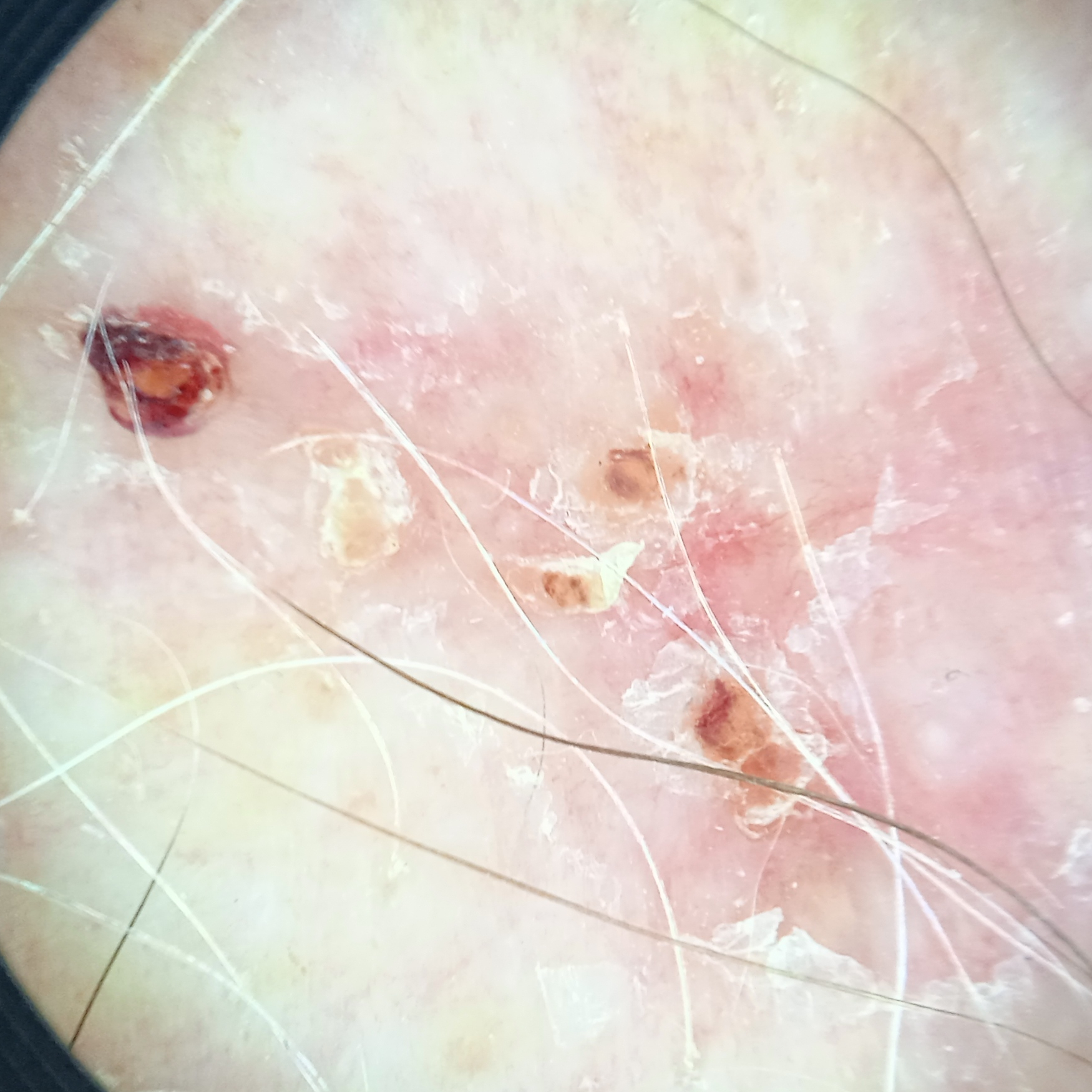Few moles overall by the patient's own estimate. The patient says their skin tans without first burning. The patient reports a personal history of skin cancer. The referring clinician suspected basal cell carcinoma. The lesion involves the torso. The lesion measures approximately 19 mm. The biopsy diagnosis was a basal cell carcinoma, following a punch biopsy, with tumor thickness 0.8 mm.